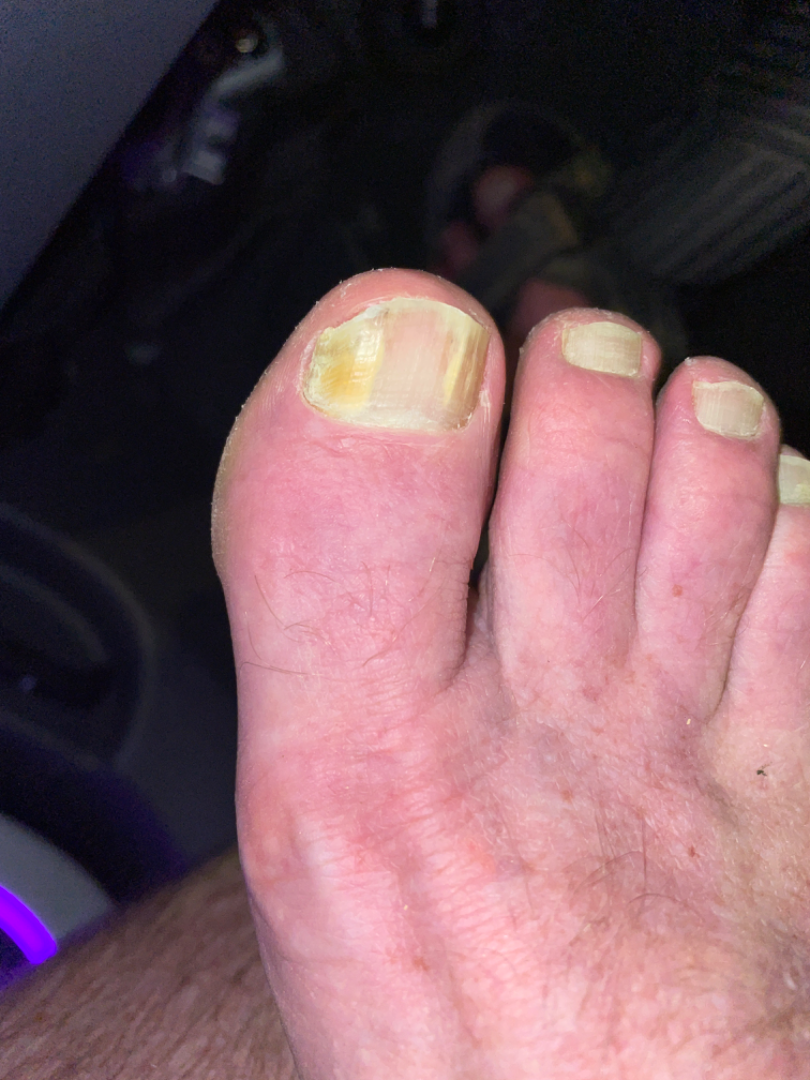Q: How long has this been present?
A: more than five years
Q: Texture?
A: flat
Q: Fitzpatrick or Monk tone?
A: Fitzpatrick phototype III
Q: What is the affected area?
A: top or side of the foot
Q: Image view?
A: close-up
Q: What conditions are considered?
A: reviewed remotely by one dermatologist: the favored diagnosis is Onychomycosis; also raised was Psoriasis; with consideration of Nail dystrophy due to trauma